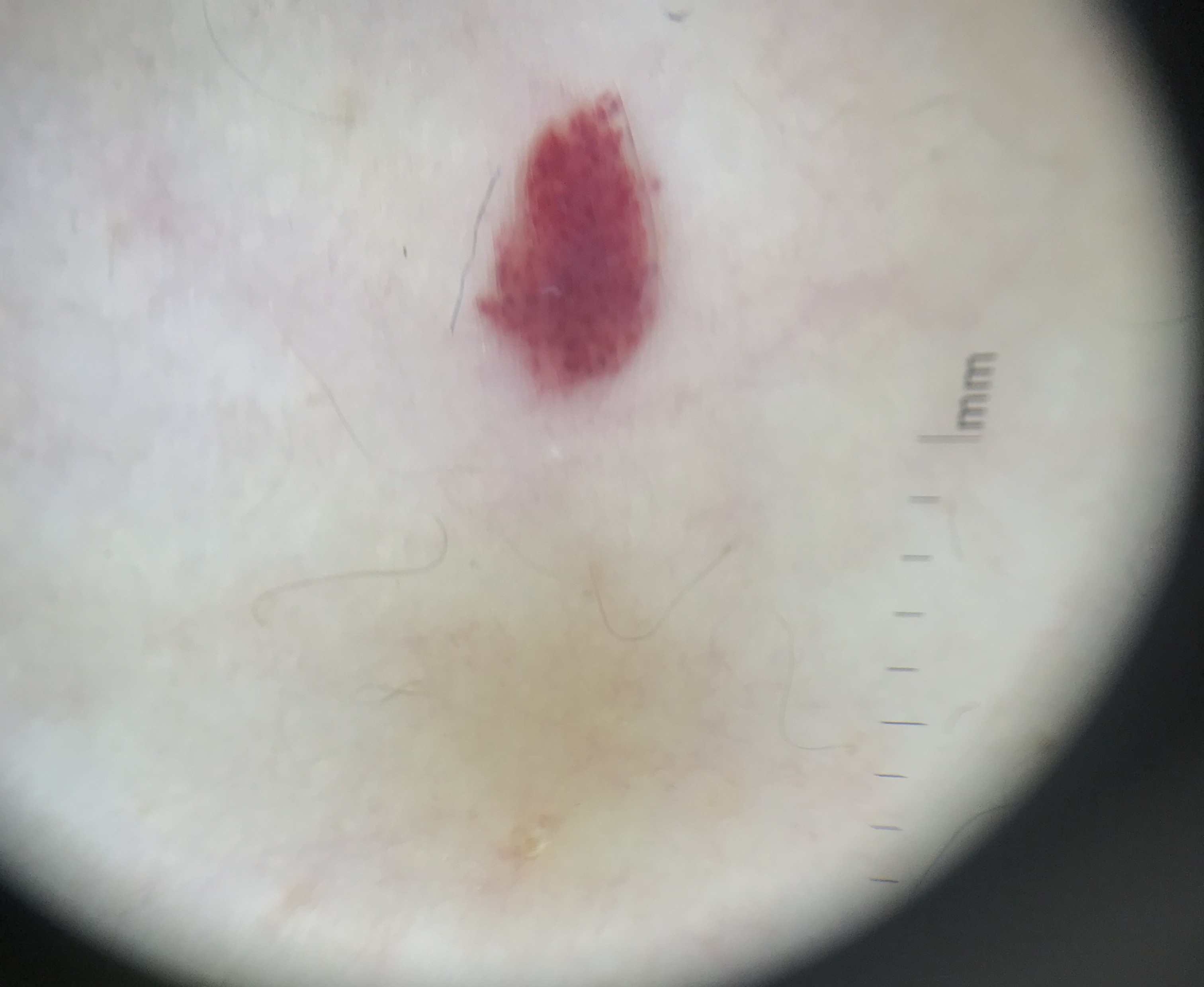Impression:
The diagnosis was a hemangioma.